An image taken at a distance. The lesion involves the arm and leg. Male contributor, age 30–39:
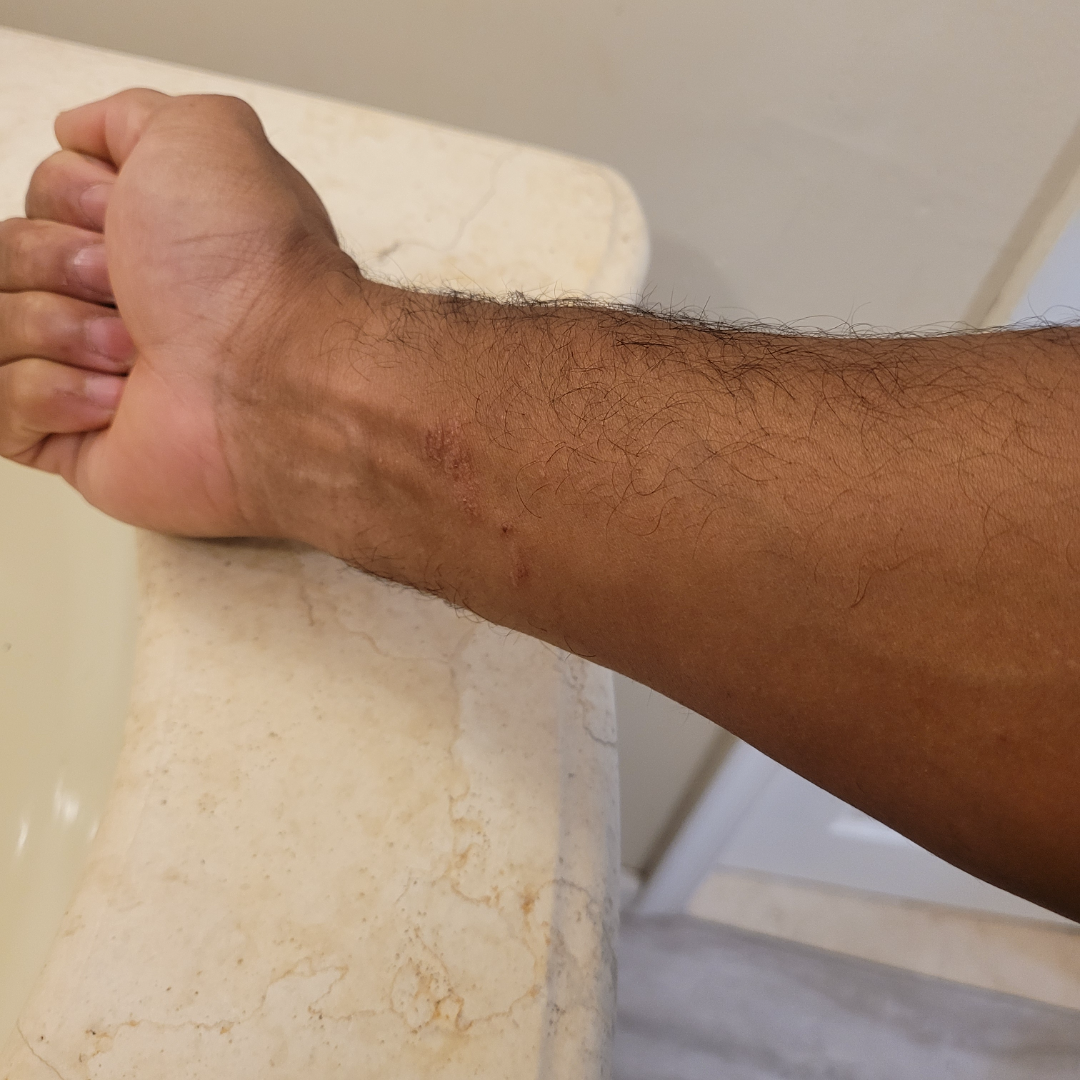Findings:
The dermatologist could not determine a likely condition from the photograph alone.